This is a close-up image · the affected area is the arm and leg · the contributor is male.
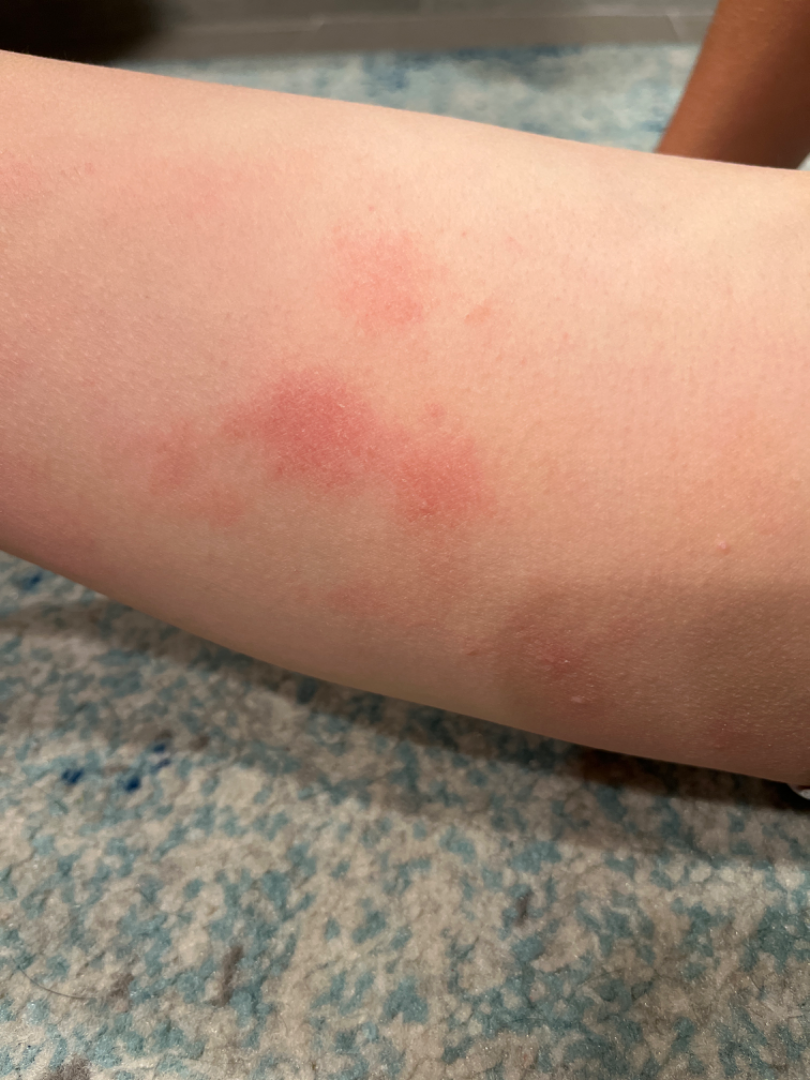Findings: On photographic review by a dermatologist: the favored diagnosis is Eczema; with consideration of Irritant Contact Dermatitis.